The photograph was taken at an angle · the lesion involves the leg · the patient considered this a rash · reported duration is one to four weeks · skin tone: Fitzpatrick II · female subject, age 18–29 · no relevant lesion symptoms reported: 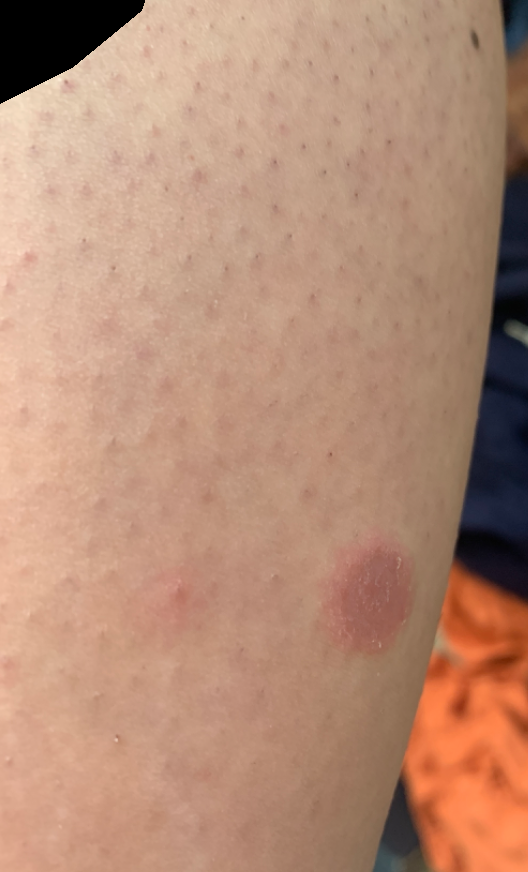Findings:
Eczema (weight 0.37); Psoriasis (weight 0.26); Tinea (weight 0.20); Pityriasis rosea (weight 0.17).